The arm is involved; this image was taken at a distance:
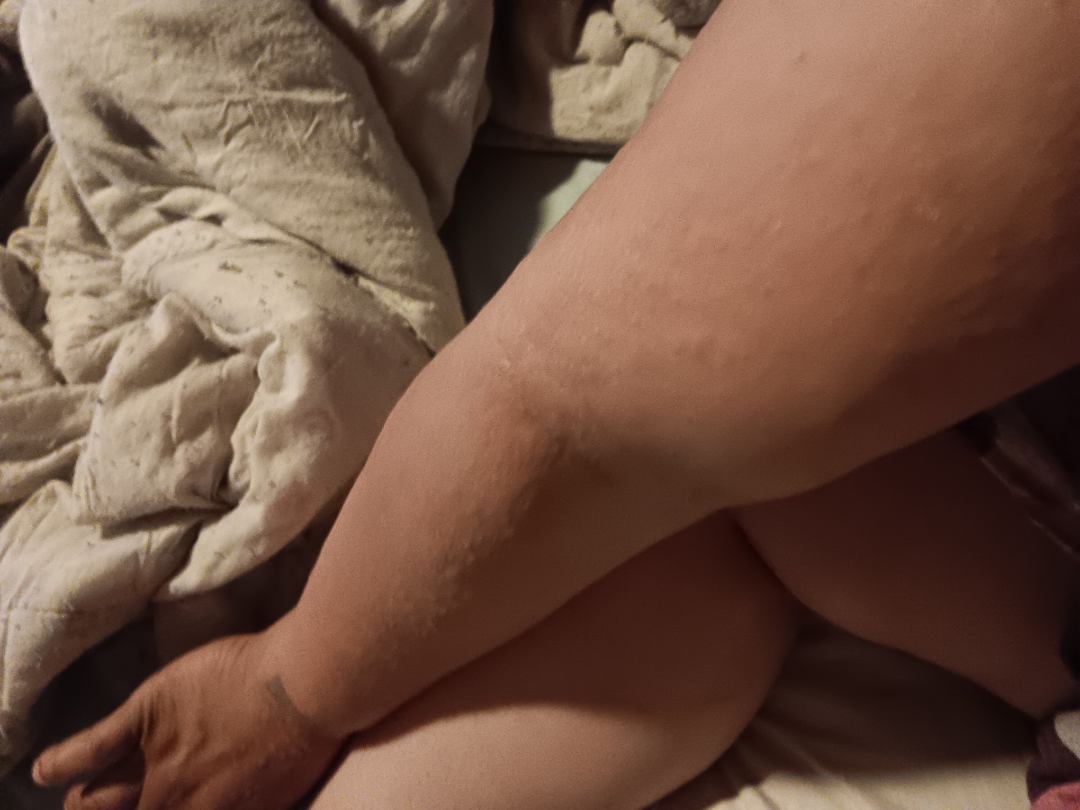Impression: The reviewer was unable to grade this case for skin condition. History: The lesion is associated with itching. No relevant systemic symptoms. The condition has been present for one to four weeks. Texture is reported as raised or bumpy.